This is a close-up image; the affected area is the arm, back of the torso, front of the torso and leg.
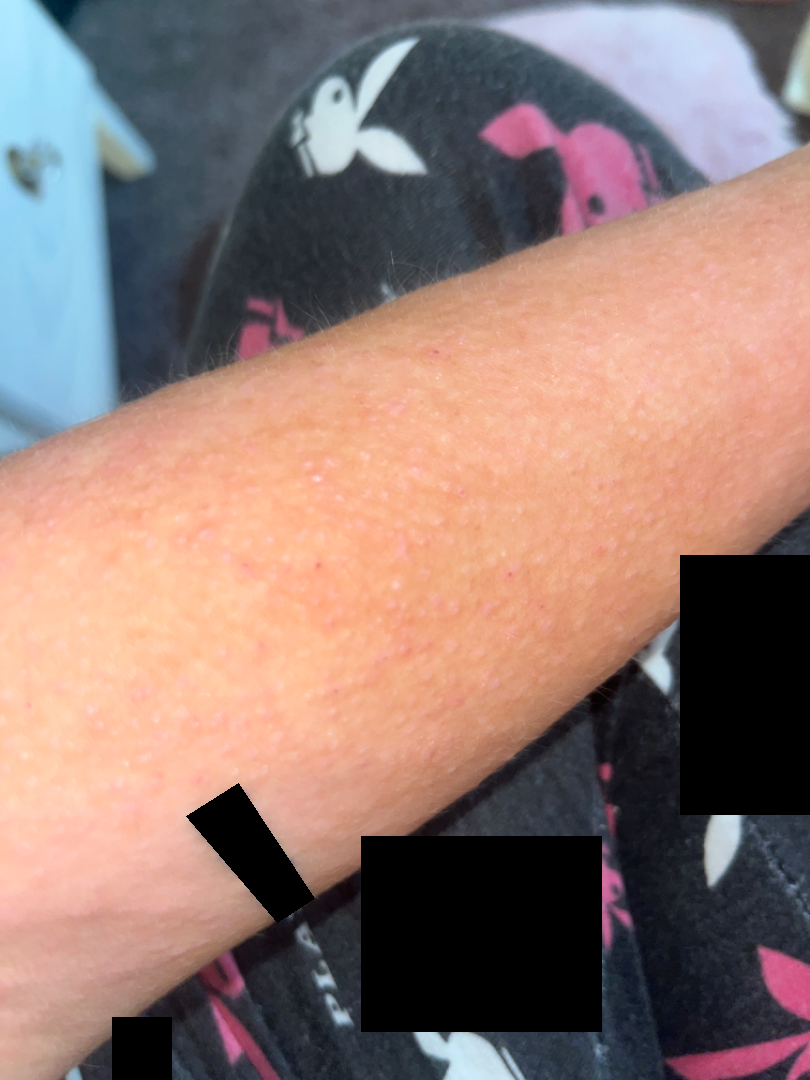Diagnostic features were not clearly distinguishable in this photograph.